A skin lesion imaged with a dermatoscope:
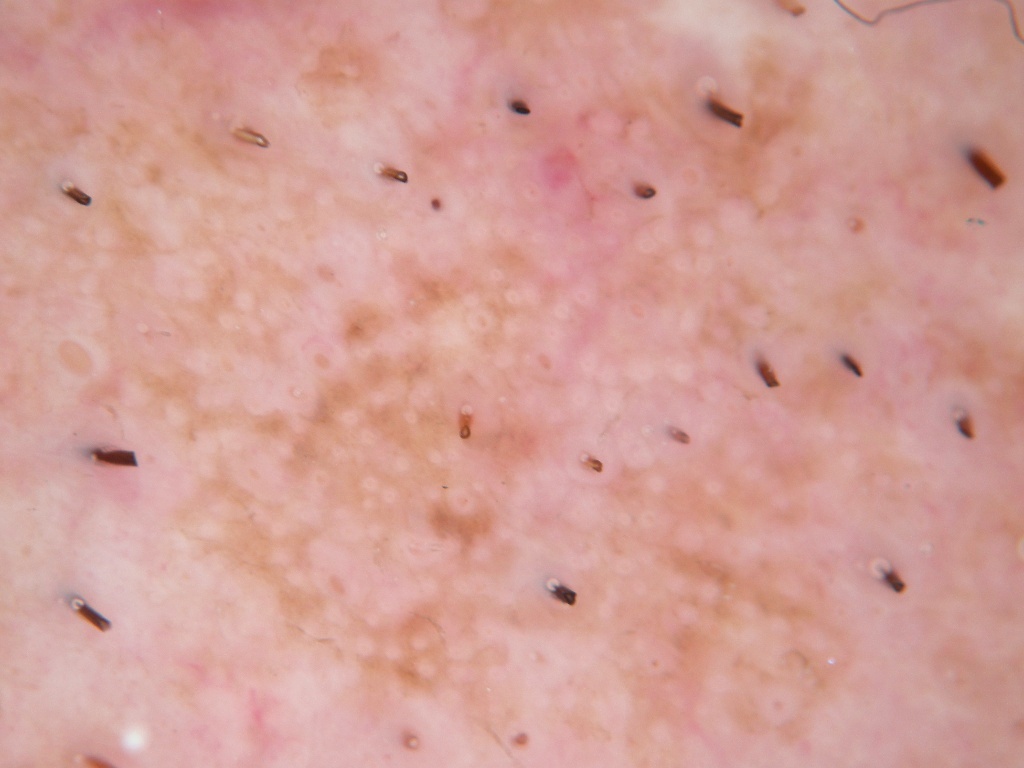The lesion spans essentially the entire dermoscopic field. Clinically diagnosed as a benign lesion.